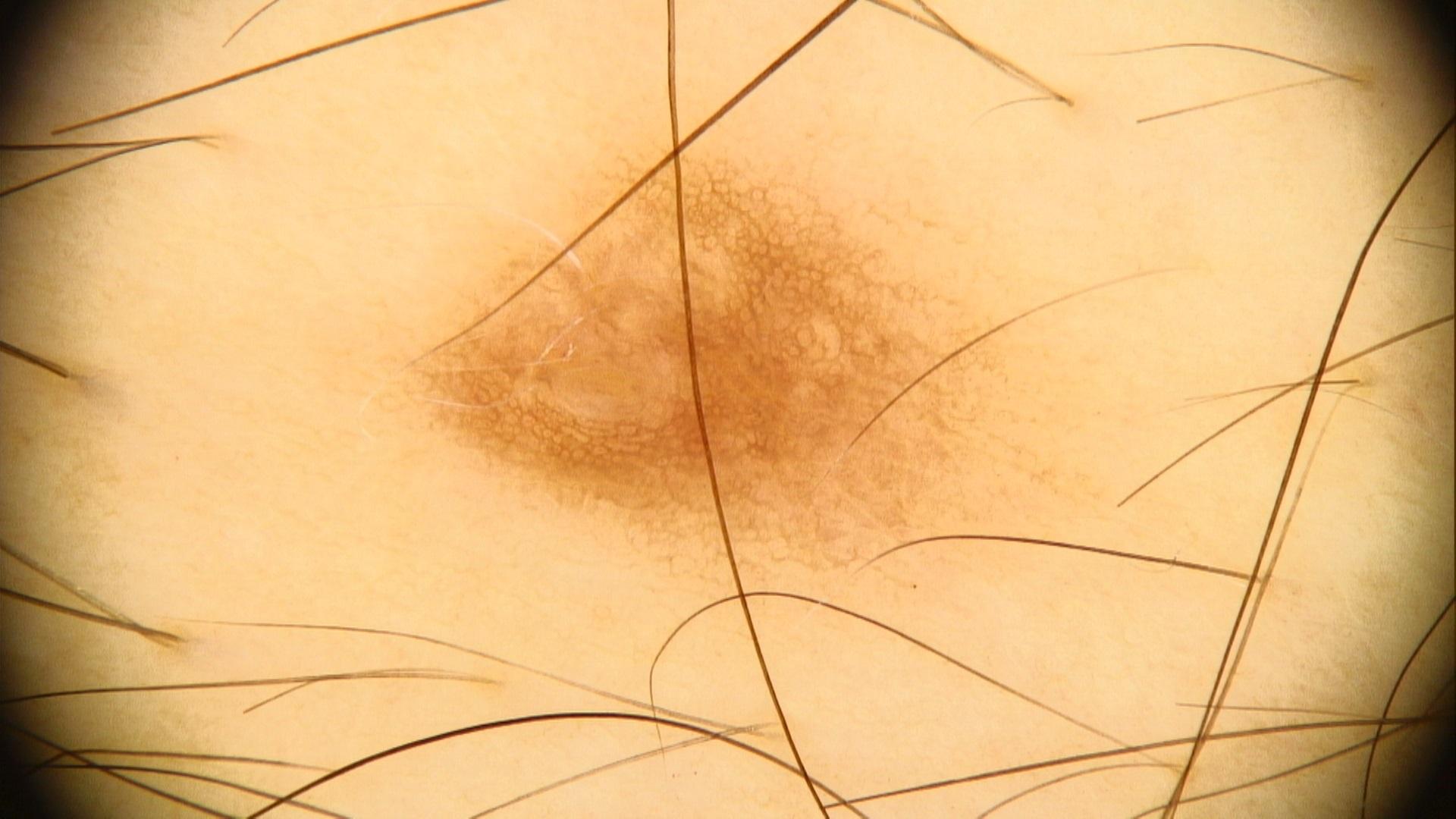| feature | finding |
|---|---|
| modality | dermatoscopic image |
| subject | male, roughly 40 years of age |
| anatomic site | the trunk |
| assessment | Nevus |